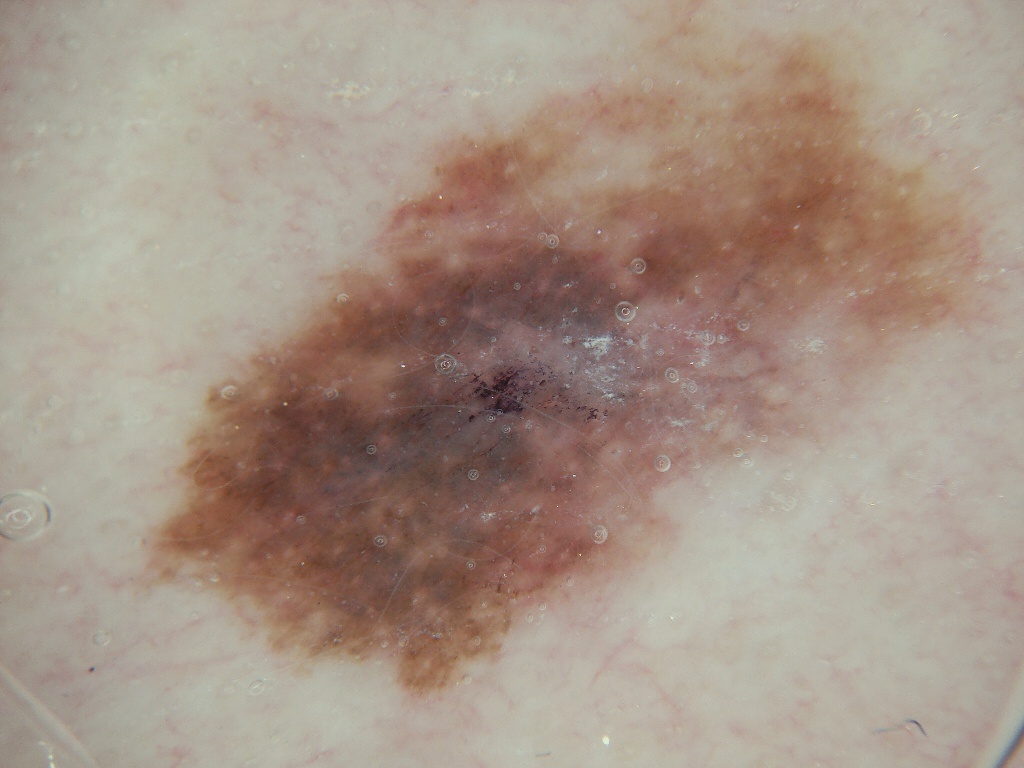patient: female, roughly 30 years of age | modality: dermatoscopic image of a skin lesion | dermoscopic features assessed but absent: streaks, globules, negative network, milia-like cysts, and pigment network | location: bbox=[115, 0, 1003, 706] | diagnosis: a melanocytic nevus, a benign skin lesion.